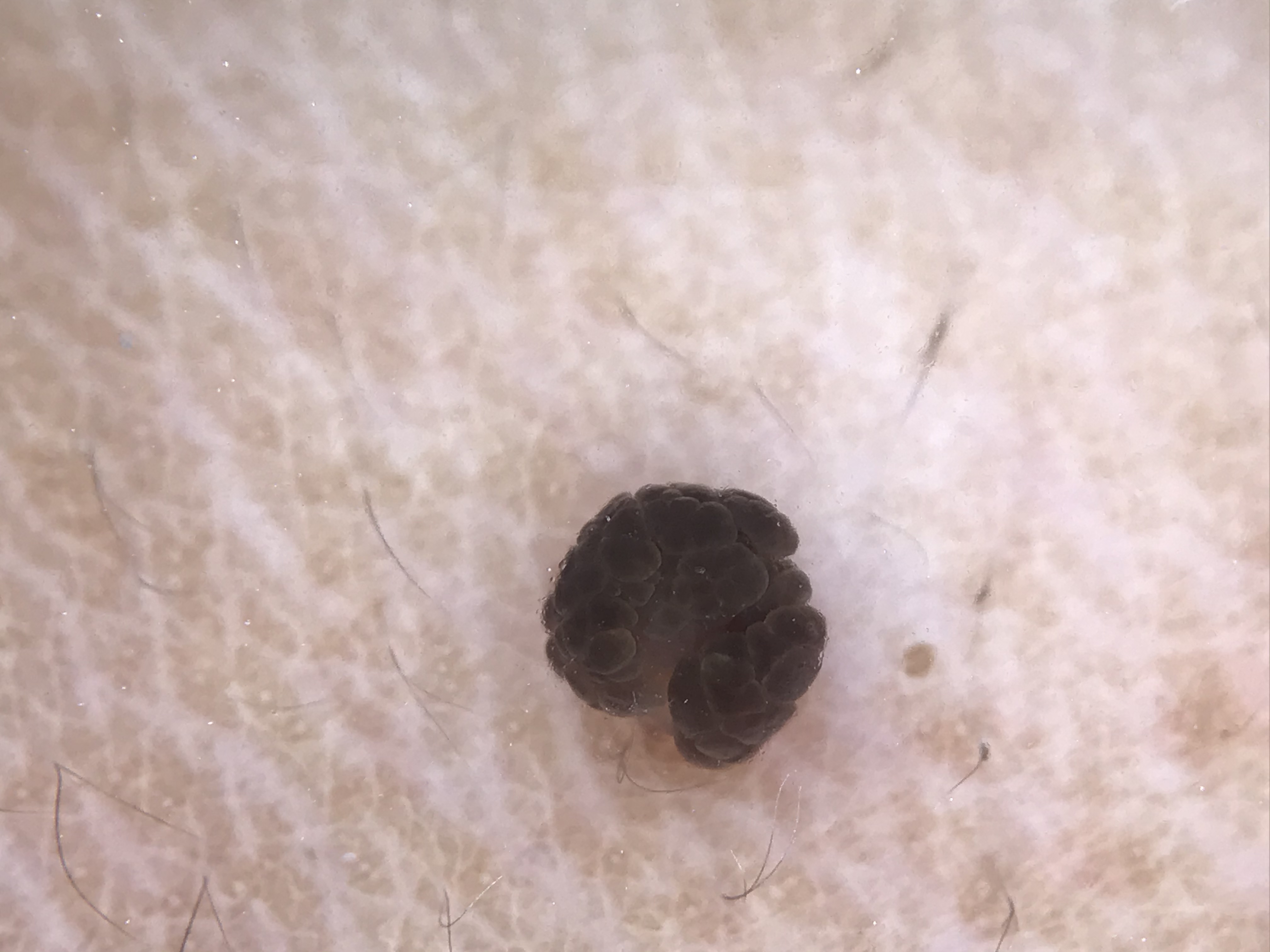image: dermatoscopy
assessment: dermal nevus (expert consensus)